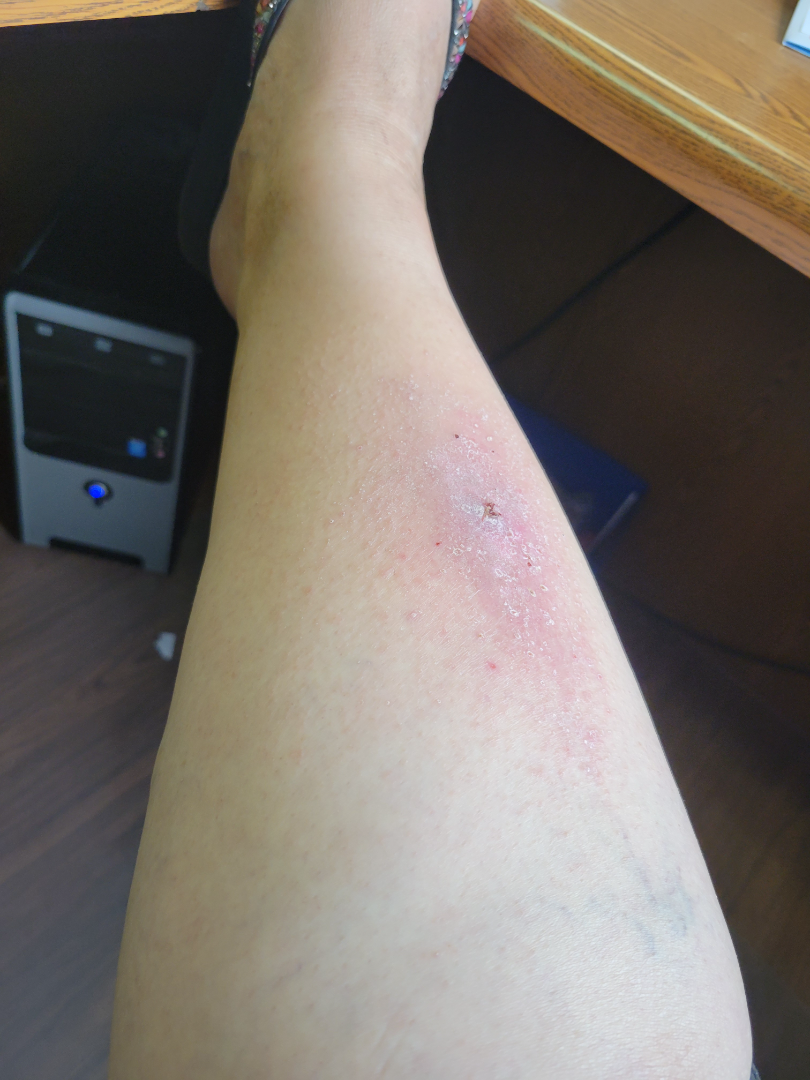anatomic site=leg | patient describes the issue as=a rash | patient-reported symptoms=enlargement, pain, bothersome appearance and burning | shot type=at a distance | present for=one to four weeks | constitutional symptoms=none reported | differential=a single dermatologist reviewed the case: most consistent with Eczema; possibly Psoriasis; also consider Allergic Contact Dermatitis.